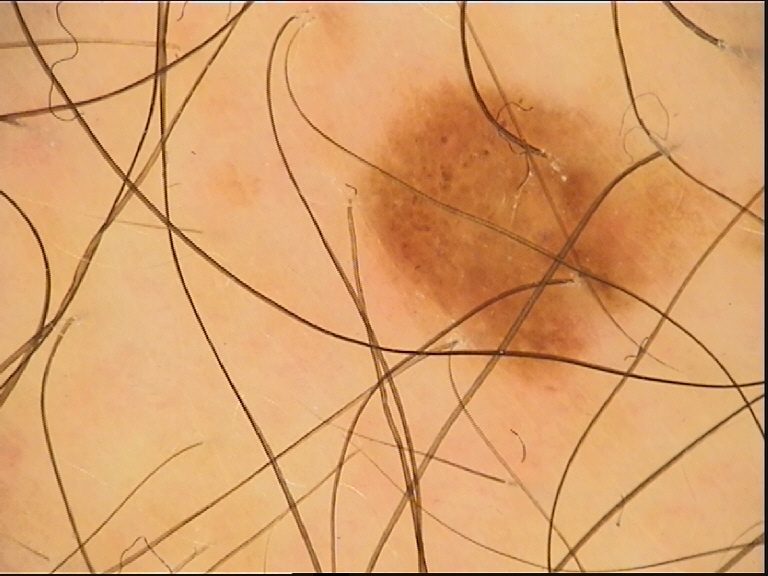Dermoscopy of a skin lesion. Classified as a dysplastic compound nevus.